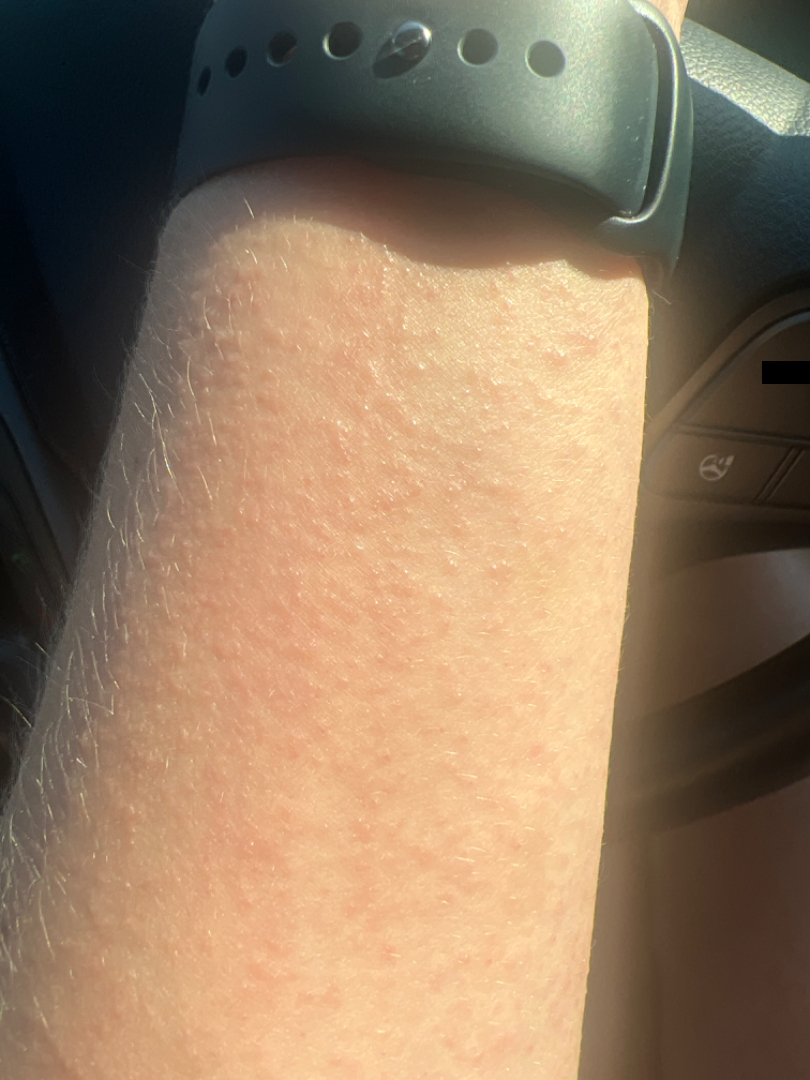Q: Patient's own categorization?
A: a rash
Q: Where on the body?
A: head or neck, leg, back of the torso, front of the torso and arm
Q: How long has this been present?
A: less than one week
Q: Reported symptoms?
A: enlargement and itching
Q: How was the photo taken?
A: close-up
Q: Patient demographics?
A: female, age 18–29
Q: How does the lesion feel?
A: fluid-filled and raised or bumpy
Q: What is the dermatologist's impression?
A: one reviewing dermatologist: the leading impression is Miliaria; possibly Eczema; with consideration of Photodermatitis